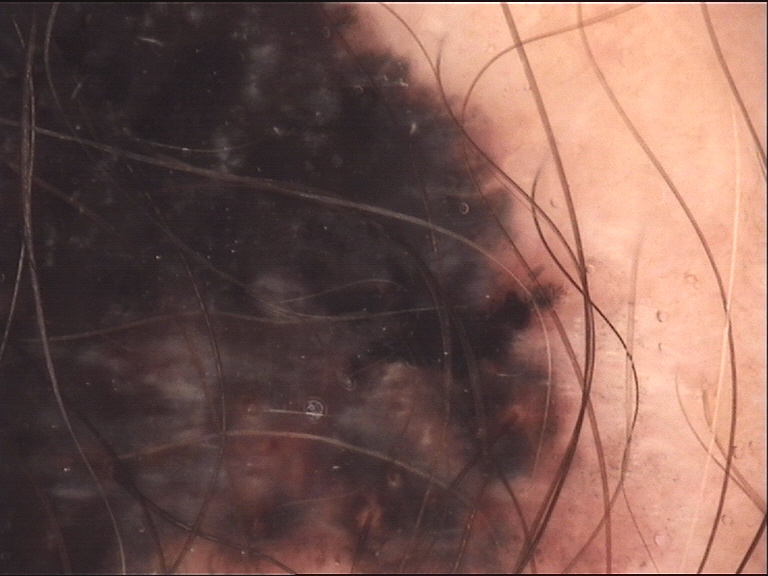A dermoscopic photograph of a skin lesion. The biopsy diagnosis was a malignant lesion — a melanoma.